A dermoscopic close-up of a skin lesion.
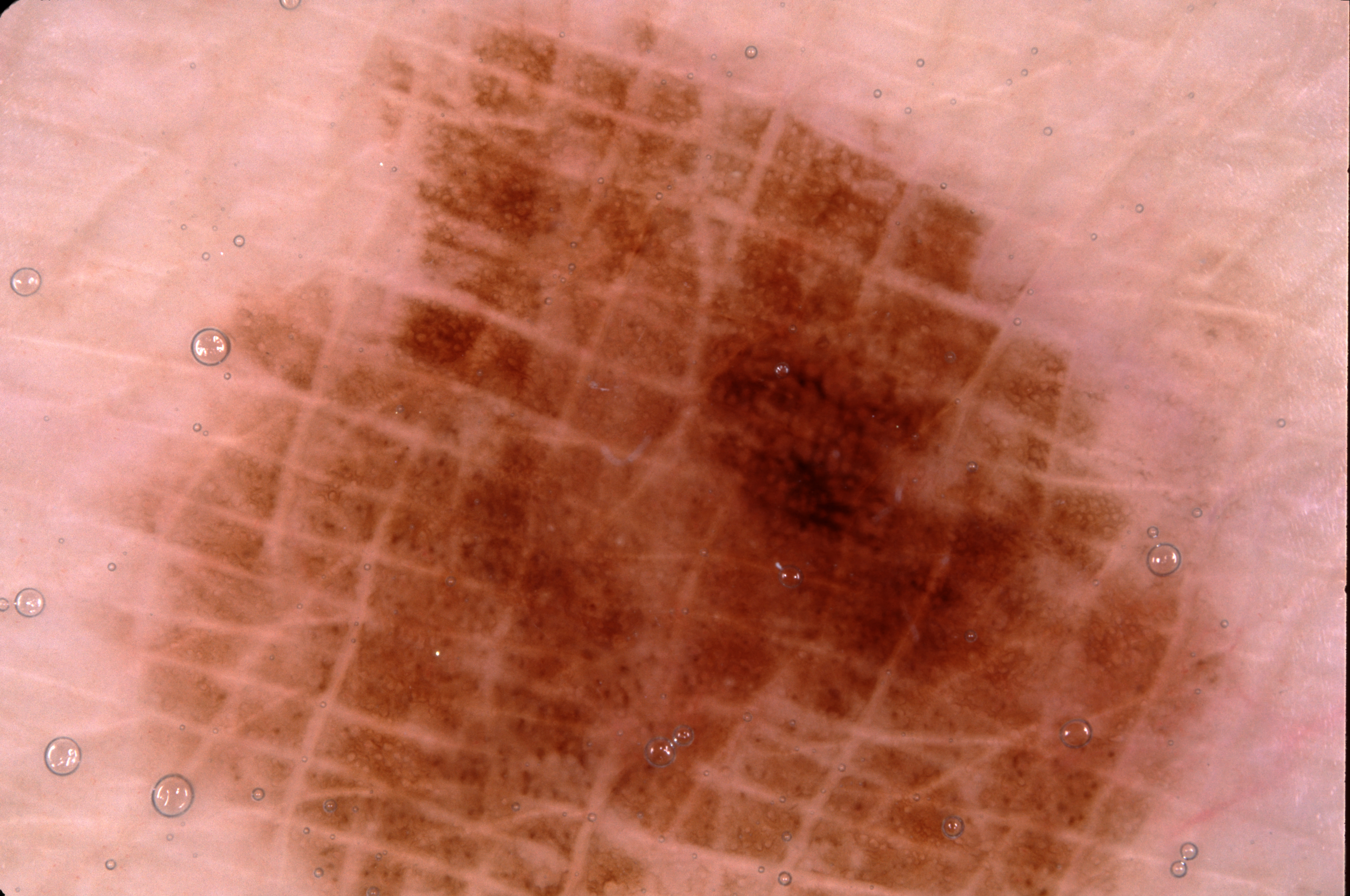features = milia-like cysts and pigment network; absent: streaks and negative network
lesion location = x1=126, y1=21, x2=1234, y2=895
lesion margin = extends past the field edge
lesion size = ~58% of the field
diagnosis = a melanoma